The patient is a female aged 48-52. Dermoscopy of a skin lesion:
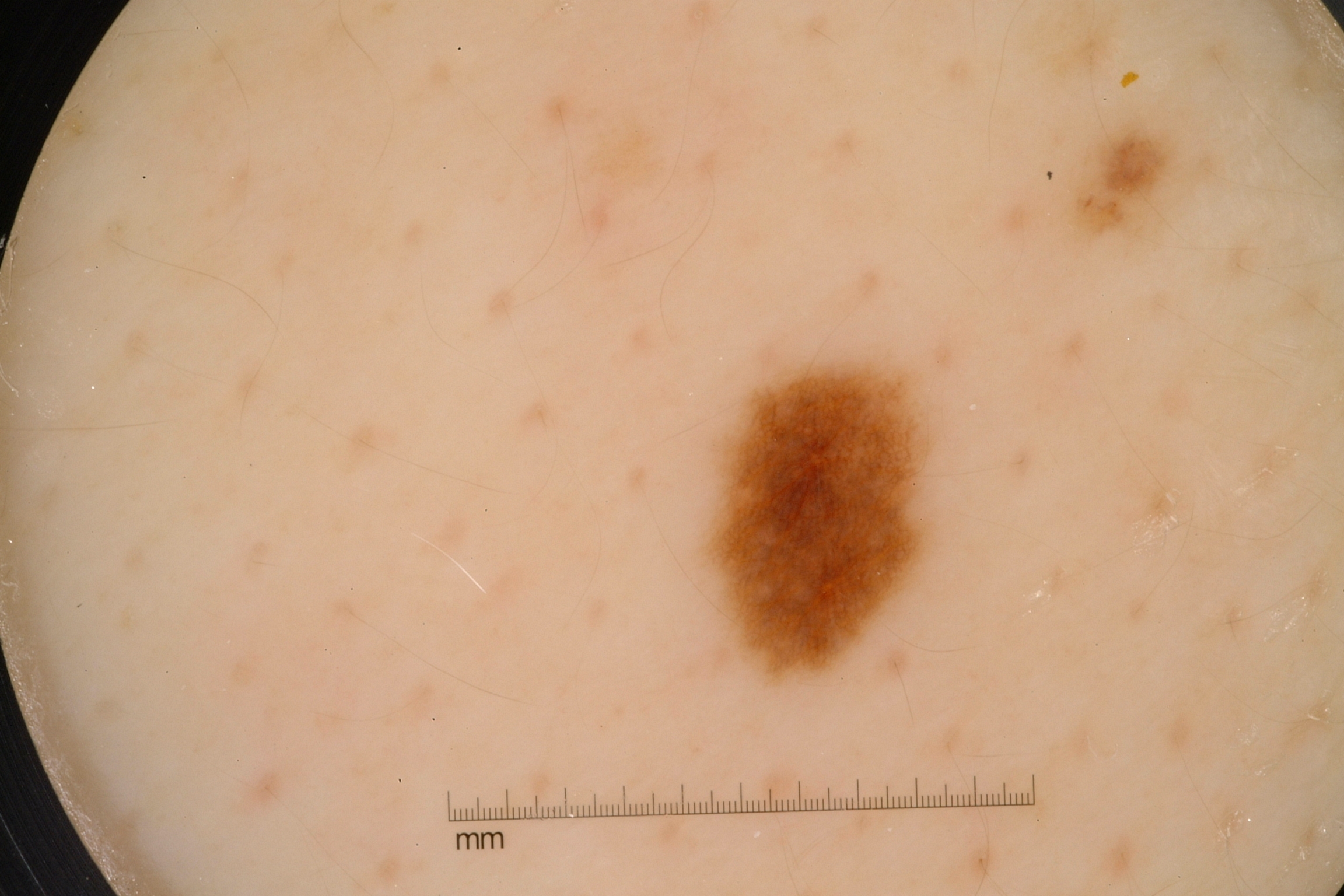A small lesion within a wider field of skin.
Dermoscopic review identifies pigment network.
As (left, top, right, bottom), the visible lesion spans <box>714, 364, 923, 672</box>.
Expert review diagnosed this as a melanocytic nevus.